Imaged for a research study, with no referral diagnosis recorded · few moles overall by the patient's own estimate · a female patient aged 84 · a dermatoscopic image of a skin lesion · the patient says their skin tans without first burning · the patient reports a personal history of cancer, no personal history of skin cancer, and no family history of skin cancer.
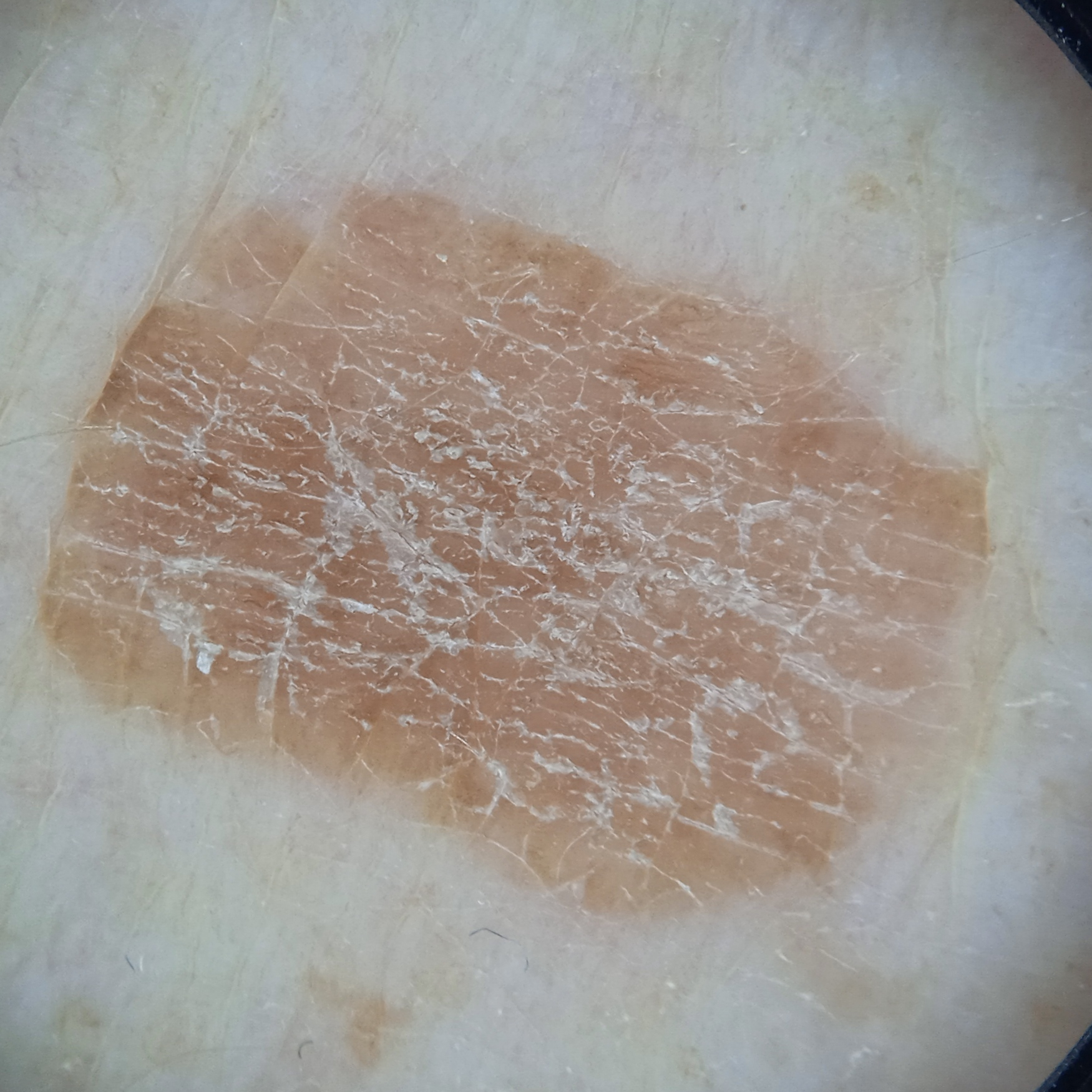| field | value |
|---|---|
| body site | an arm |
| diameter | 11.2 mm |
| assessment | seborrheic keratosis (dermatologist consensus) |